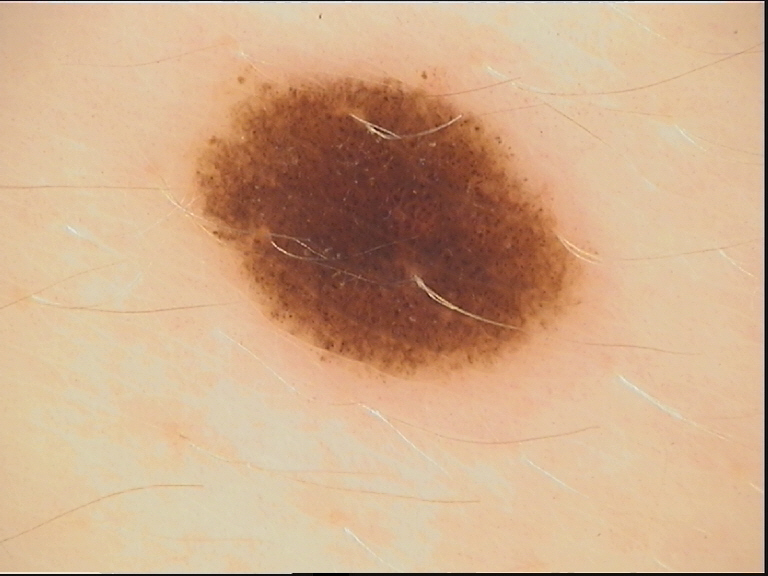Dermoscopy of a skin lesion.
Diagnosed as a benign lesion — a dysplastic junctional nevus.